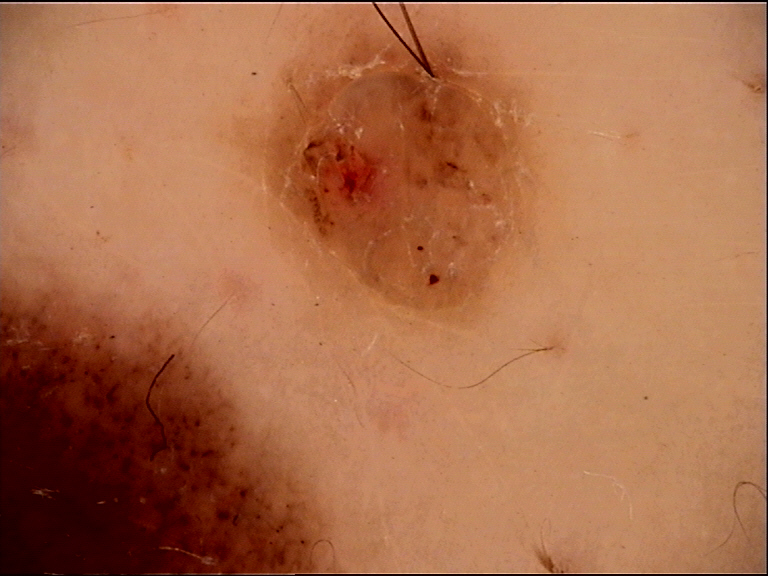Q: What kind of lesion is this?
A: banal
Q: What was the diagnostic impression?
A: dermal nevus (expert consensus)